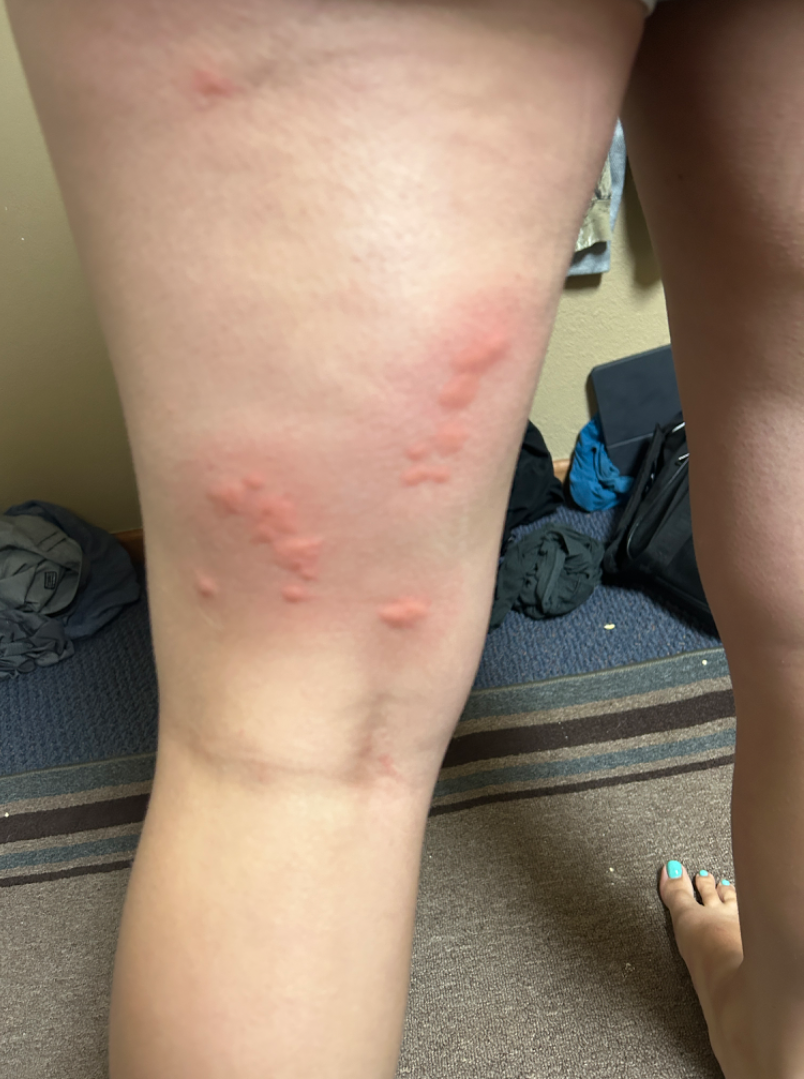Clinical context: The leg is involved. Texture is reported as raised or bumpy. Symptoms reported: itching, pain and enlargement. This is a close-up image. No associated systemic symptoms reported. Assessment: On remote dermatologist review: favoring Urticaria; also raised was Insect Bite; an alternative is Allergic Contact Dermatitis.